Close-up view, the condition has been present for less than one week, the patient is a female aged 50–59, the leg is involved, no associated systemic symptoms reported, reported lesion symptoms include itching.
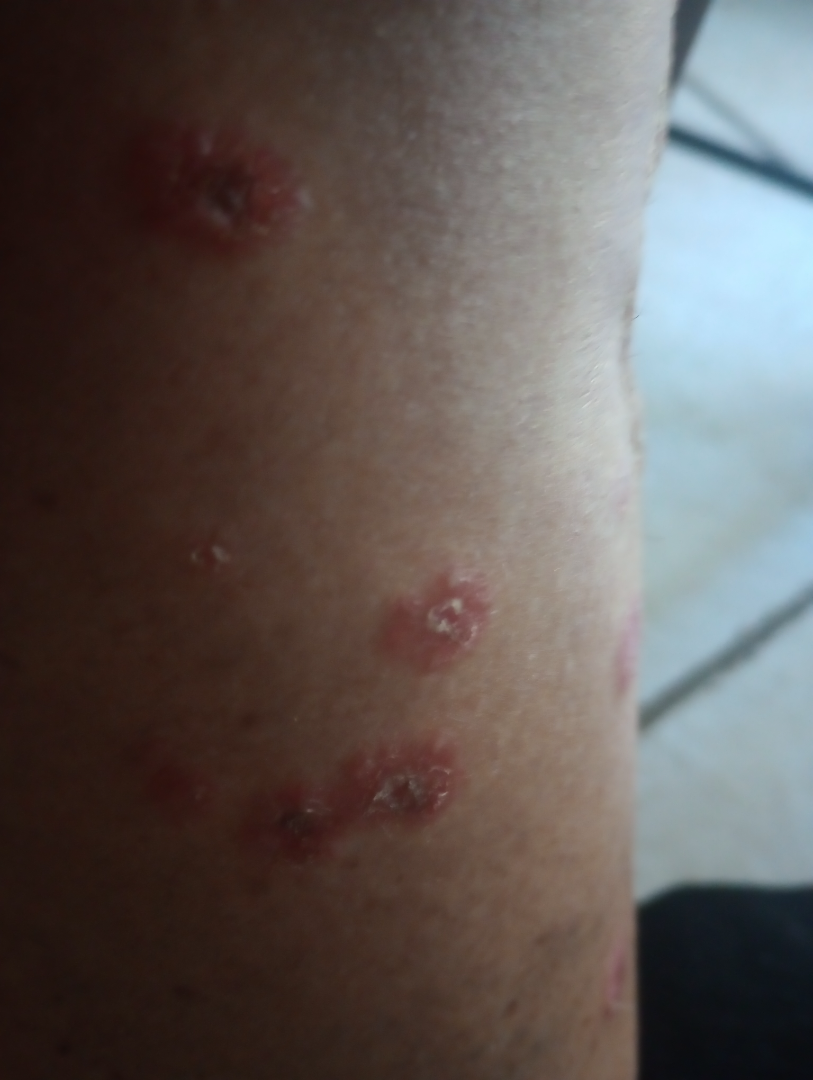Diagnostic features were not clearly distinguishable in this photograph.